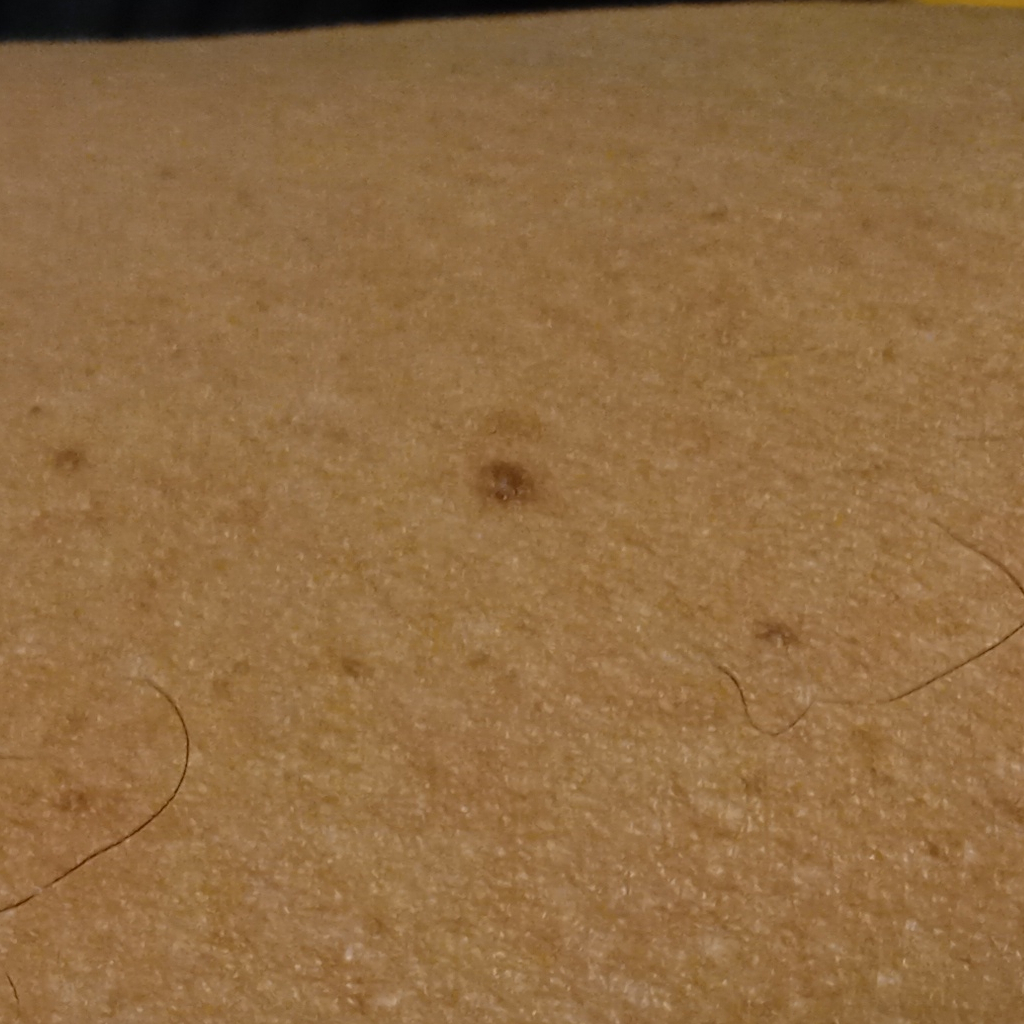<lesion>
<patient>
<age>54</age>
<sex>male</sex>
</patient>
<referral>research study (no referral diagnosis)</referral>
<image>clinical photograph</image>
<risk_factors>
<positive>a personal history of cancer</positive>
</risk_factors>
<sun_reaction>skin tans without first burning</sun_reaction>
<diagnosis>
<name>melanocytic nevus</name>
<malignancy>benign</malignancy>
</diagnosis>
</lesion>